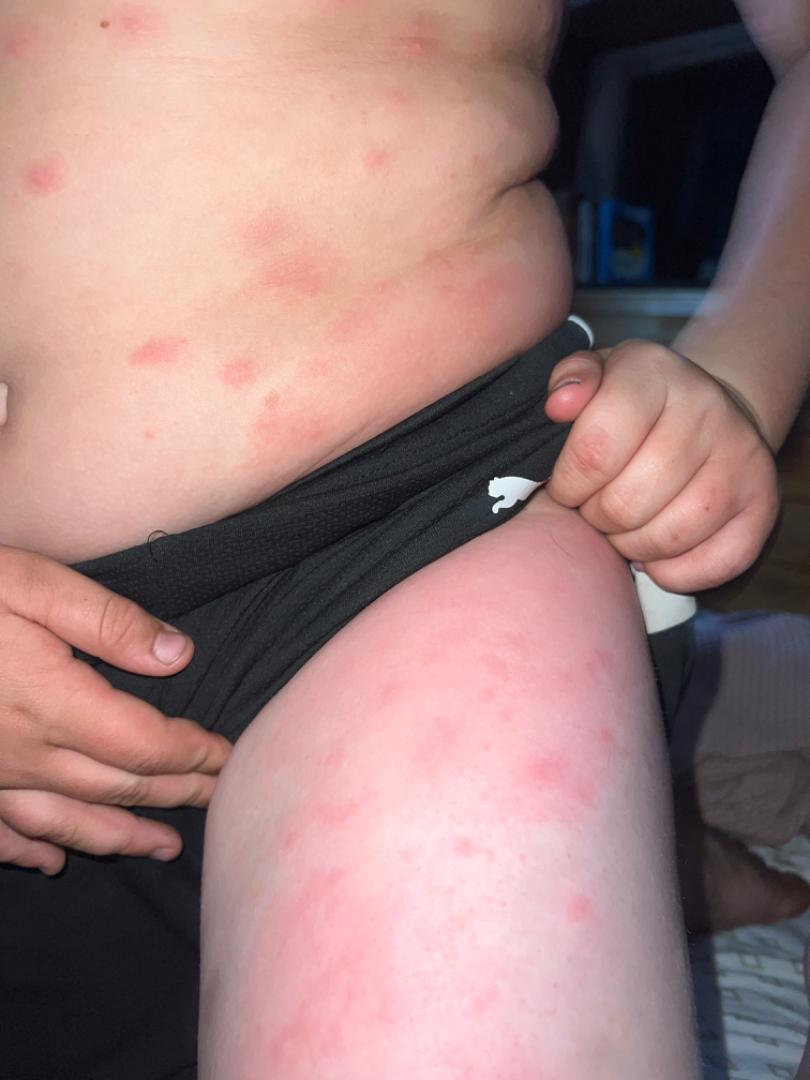The affected area is the front of the torso, leg and arm. The patient described the issue as a rash. Fitzpatrick skin type III; human graders estimated 2 on the Monk Skin Tone. The subject is 18–29, male. This image was taken at an angle. Texture is reported as raised or bumpy. Present for about one day. On remote review of the image: the differential is split between Cellulitis and Allergic Contact Dermatitis.